The chart records pesticide exposure and alcohol use; a male subject aged 58; a clinical photograph of a skin lesion; Fitzpatrick II:
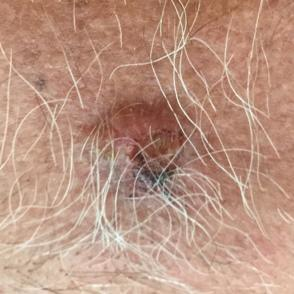{
  "lesion_location": "the chest",
  "lesion_size": {
    "diameter_1_mm": 20.0,
    "diameter_2_mm": 18.0
  },
  "symptoms": {
    "present": [
      "itching",
      "elevation",
      "pain",
      "growth",
      "bleeding"
    ],
    "absent": [
      "change in appearance"
    ]
  },
  "diagnosis": {
    "name": "basal cell carcinoma",
    "code": "BCC",
    "malignancy": "malignant",
    "confirmation": "histopathology"
  }
}